The leg is involved; the patient is 18–29, female; the photo was captured at a distance:
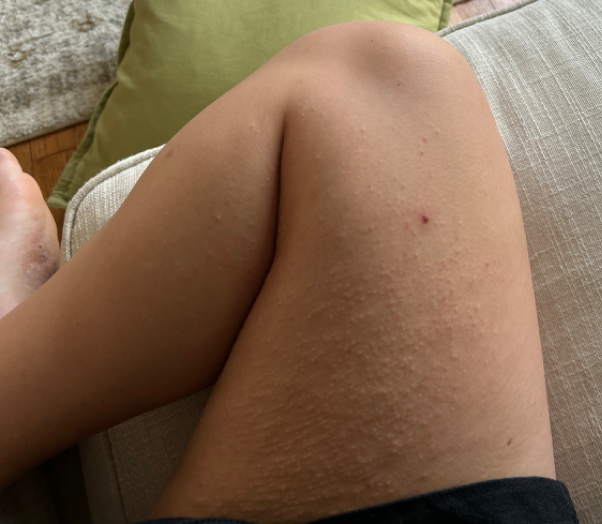Assessment: The dermatologist could not determine a likely condition from the photograph alone.